A patient aged 80; a clinical photograph of a skin lesion.
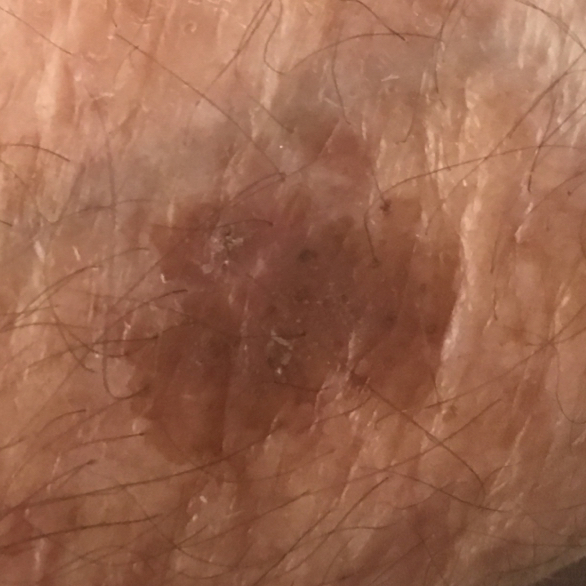Clinical context:
The patient reports that the lesion has not grown and does not hurt.
Conclusion:
Expert review favored a benign lesion — a seborrheic keratosis.